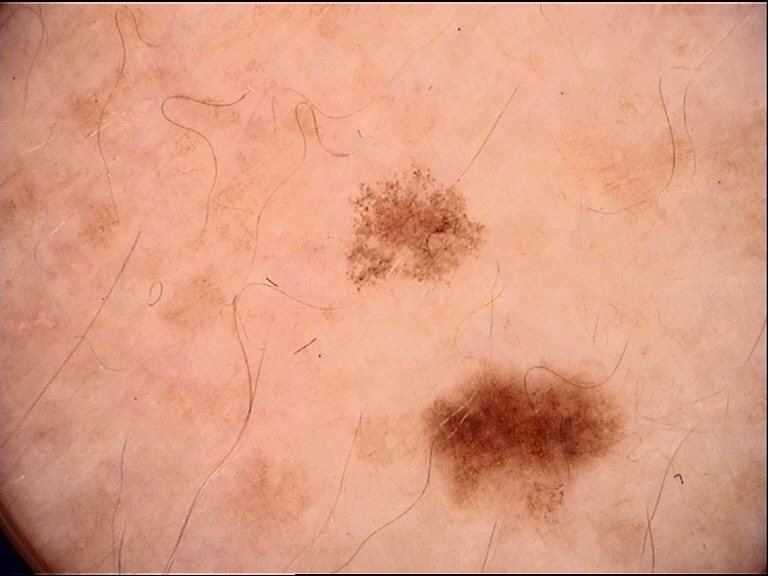A dermoscopic image of a skin lesion. The diagnosis was a dysplastic junctional nevus.